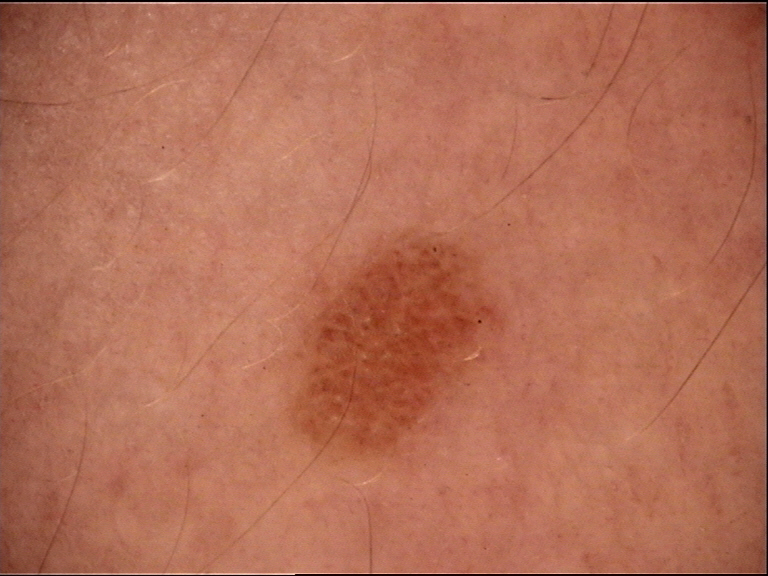A dermoscopy image of a single skin lesion. The morphology is that of a banal lesion. The diagnostic label was a compound nevus.